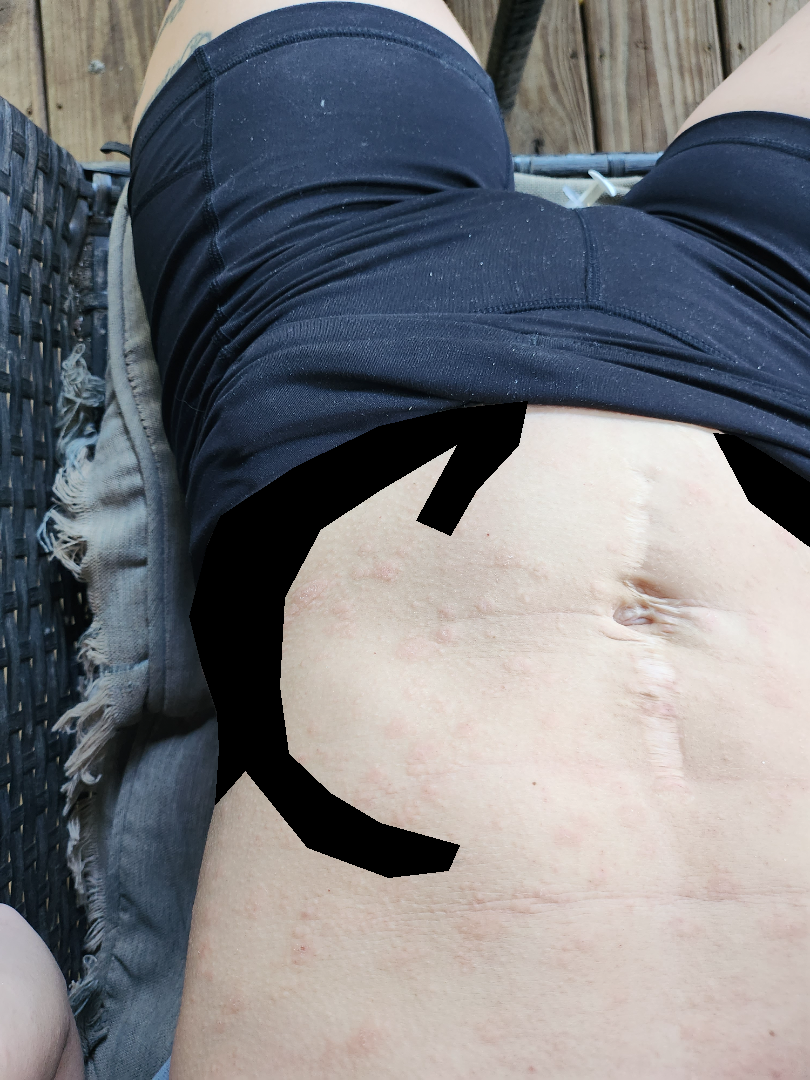assessment = could not be assessed
location = back of the torso, arm, head or neck and front of the torso
shot type = at a distance